Located on the arm · close-up view: 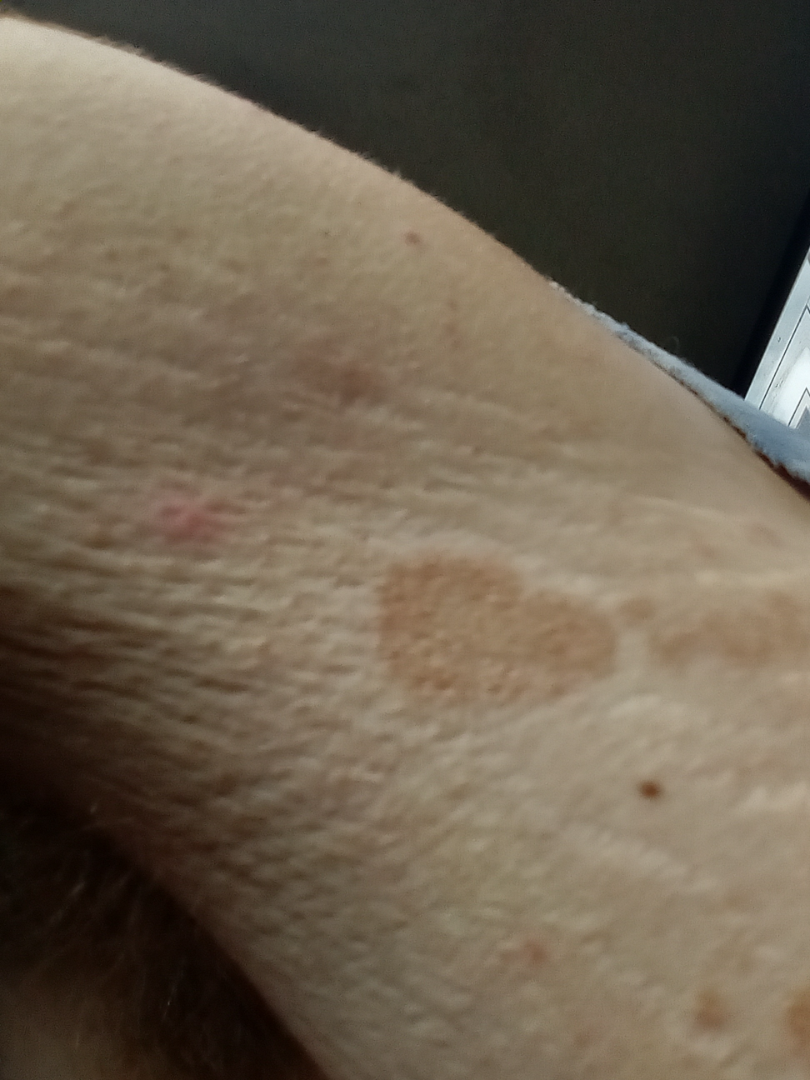The reviewer was unable to grade this case for skin condition.